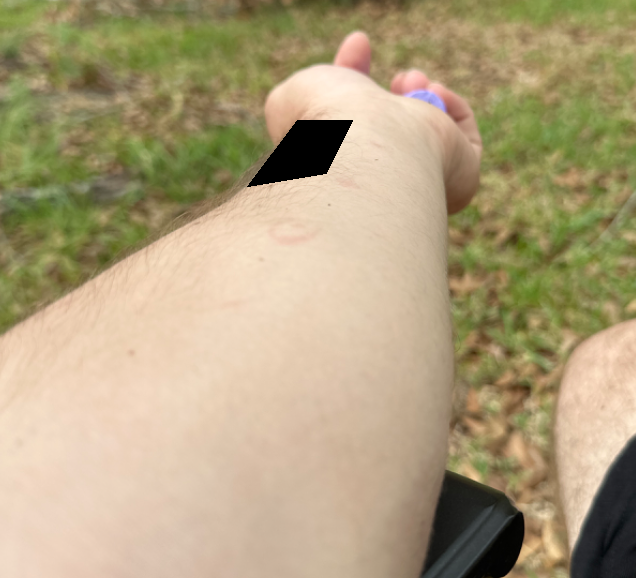  assessment: not assessable
  symptoms: bothersome appearance
  shot_type: at an angle
  duration: about one day
  body_site: arm
  texture: flat